This is a close-up image, the affected area is the palm and back of the hand: 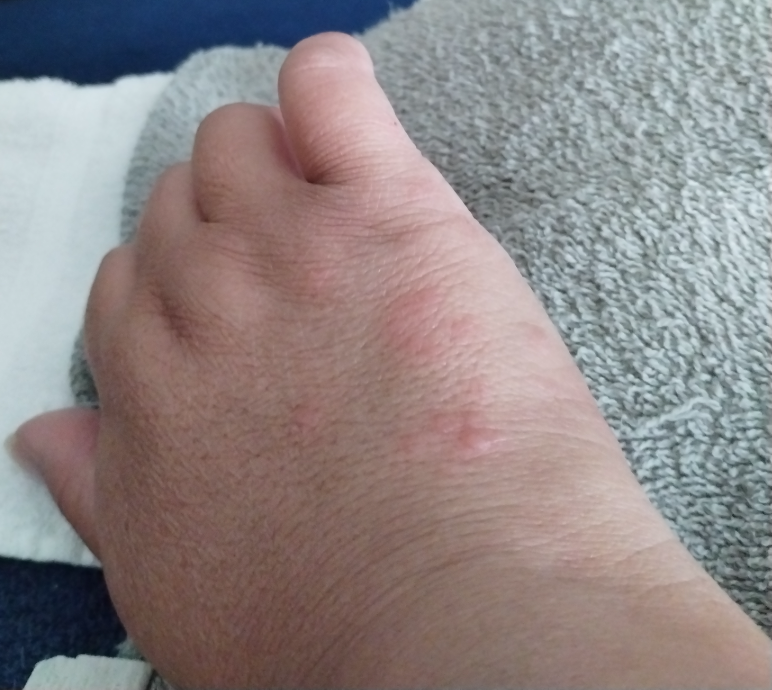differential = one reviewing dermatologist: the leading consideration is Urticaria; possibly Granuloma annulare.